A dermoscopy image of a single skin lesion. A male patient in their mid-60s: 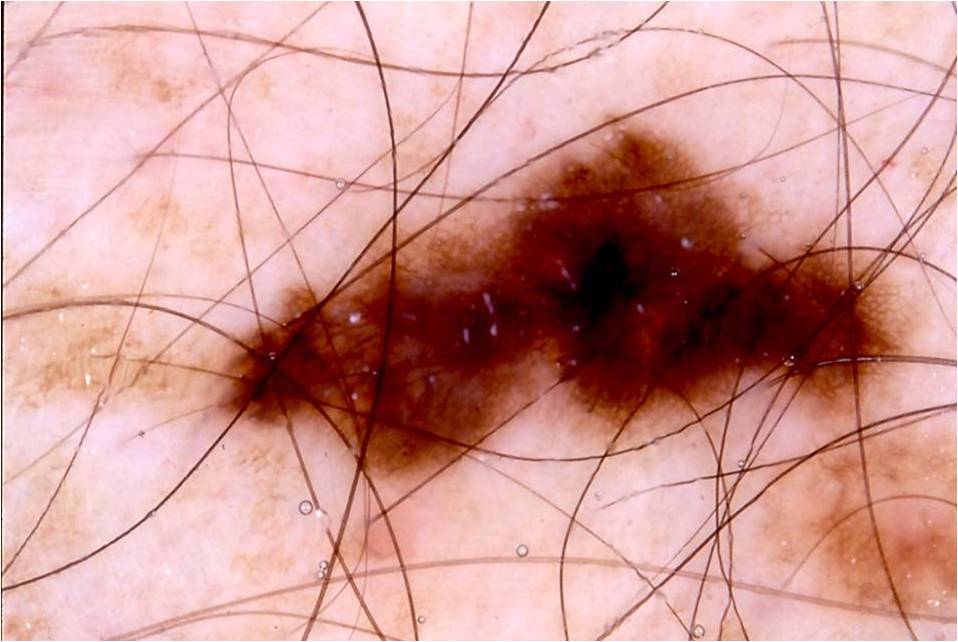As (left, top, right, bottom), the lesion occupies the region box(211, 115, 920, 491). The lesion occupies roughly 25% of the field. Dermoscopic review identifies pigment network. The clinical diagnosis was a melanocytic nevus, a benign lesion.